A skin lesion imaged with a dermatoscope.
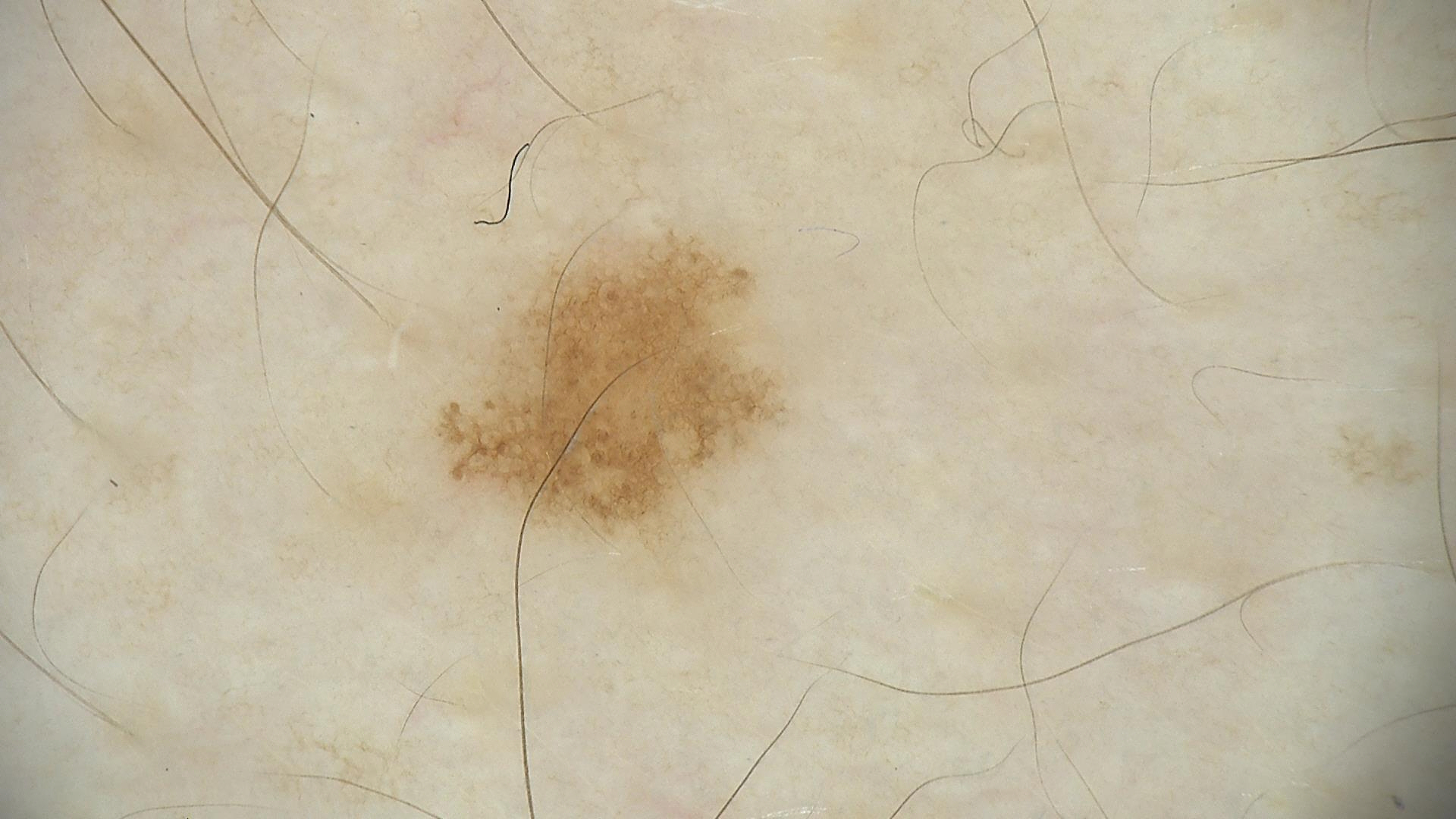diagnostic label — dysplastic junctional nevus (expert consensus).